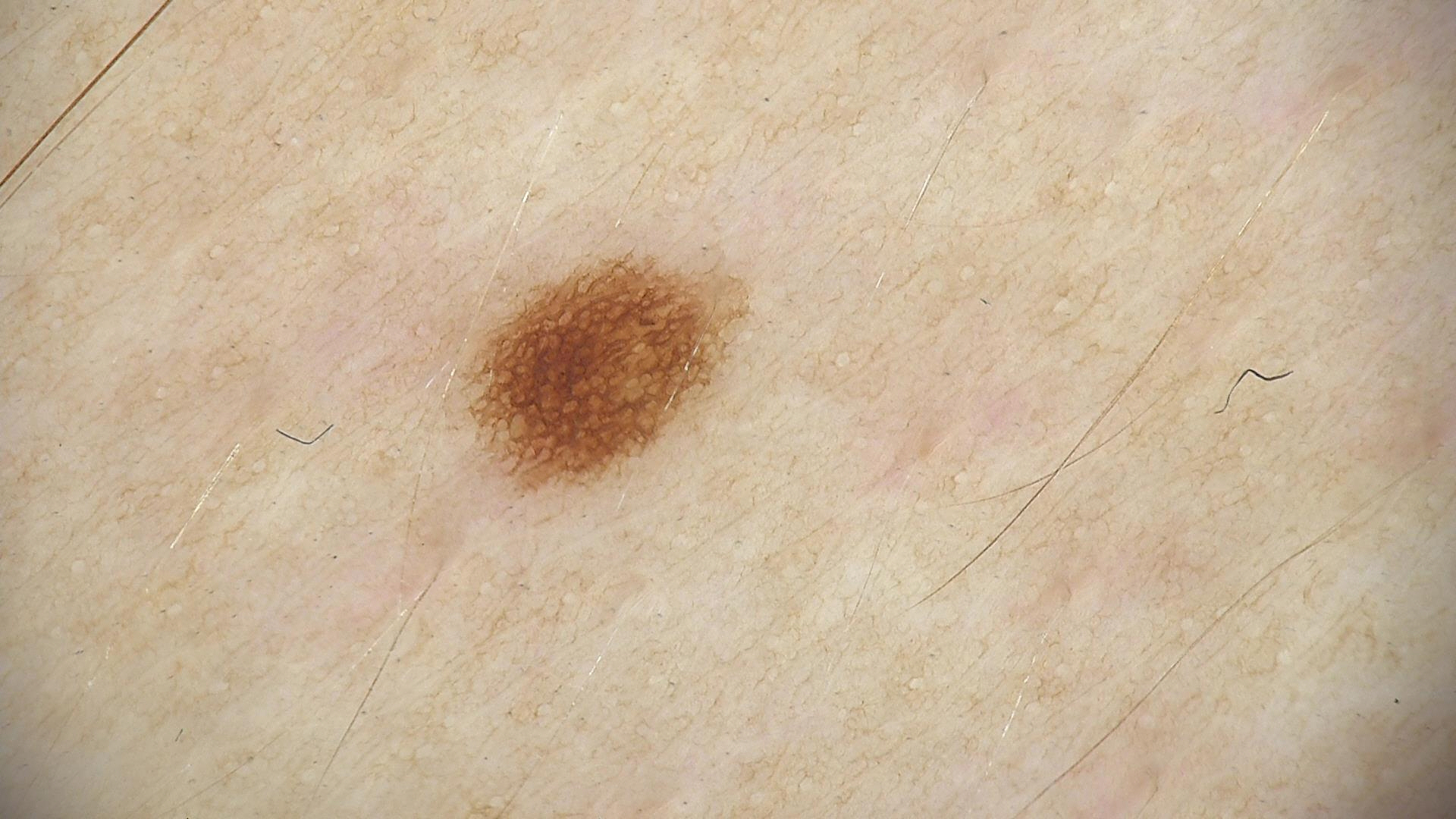A dermoscopic image of a skin lesion. Diagnosed as a dysplastic junctional nevus.